A skin lesion imaged with a dermatoscope: 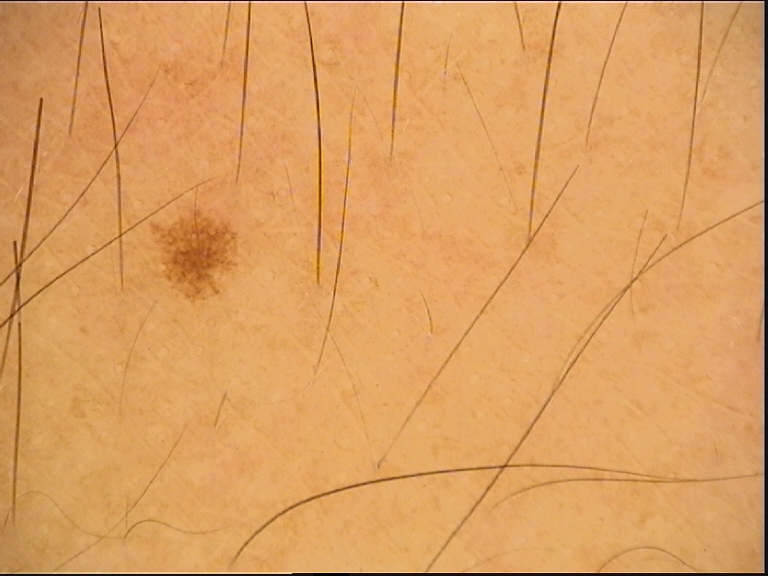Labeled as a benign lesion — a dysplastic junctional nevus.